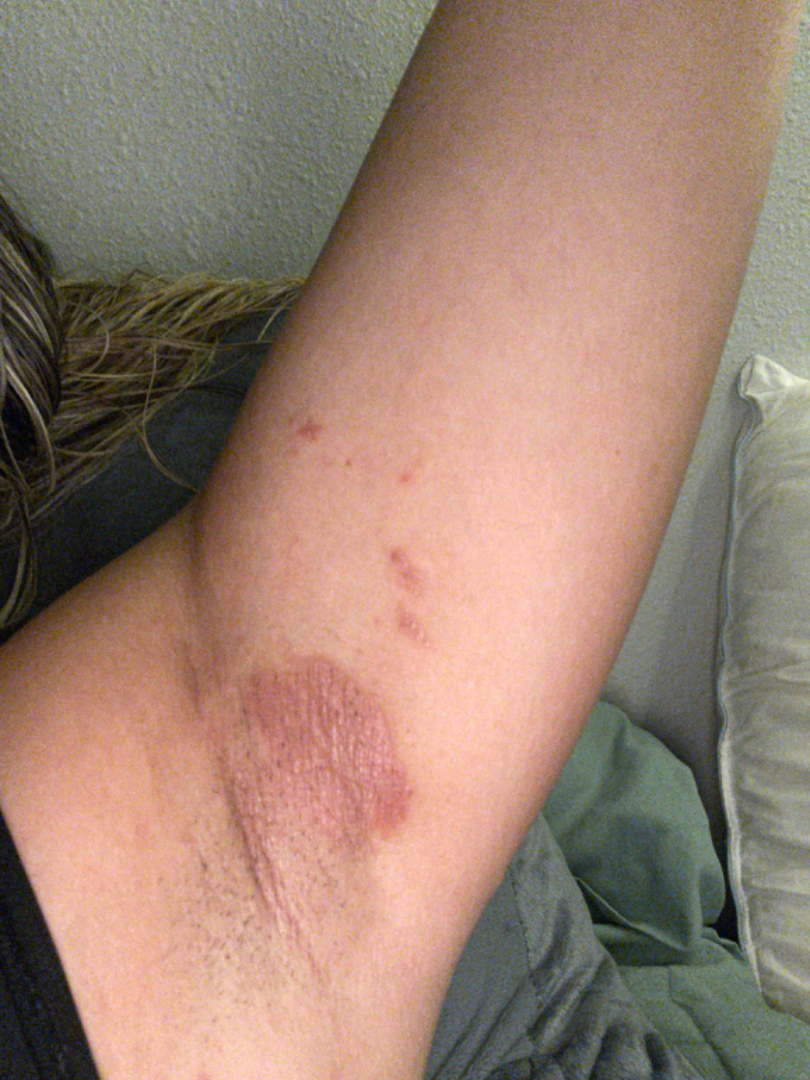Clinical context: The contributor notes itching and bothersome appearance. The condition has been present for three to twelve months. Self-categorized by the patient as a rash. The patient is female. This is a close-up image. No constitutional symptoms were reported. Texture is reported as rough or flaky. Assessment: On remote review of the image: Allergic Contact Dermatitis and Irritant Contact Dermatitis were each considered, in no particular order.